A dermatoscopic image of a skin lesion.
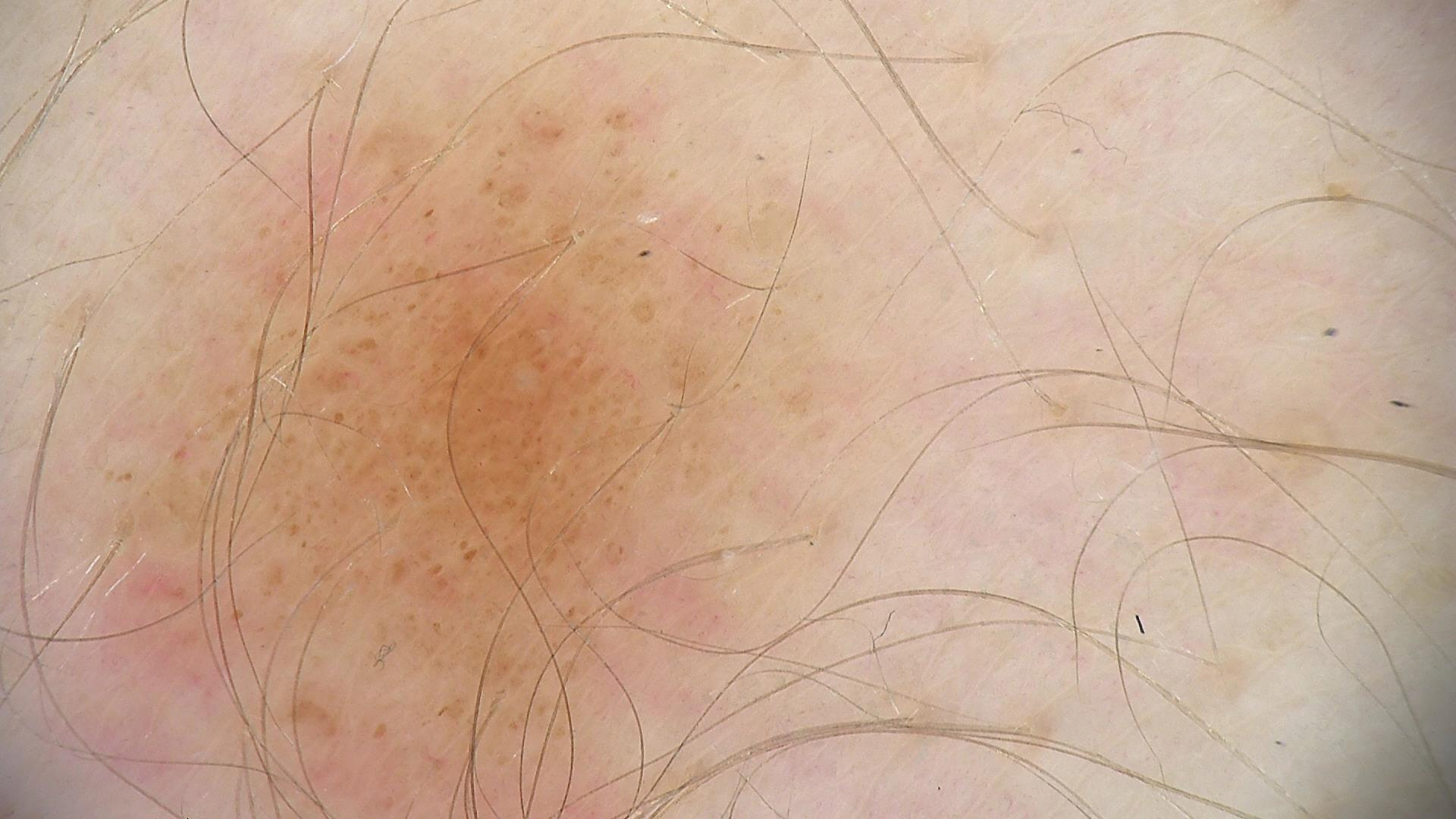class — compound nevus (expert consensus).